Collected as part of a research study, without a referral diagnosis. Few moles overall by the patient's own estimate. A skin lesion imaged with a dermatoscope. The patient says their skin reddens with sun exposure. A male patient age 62 — 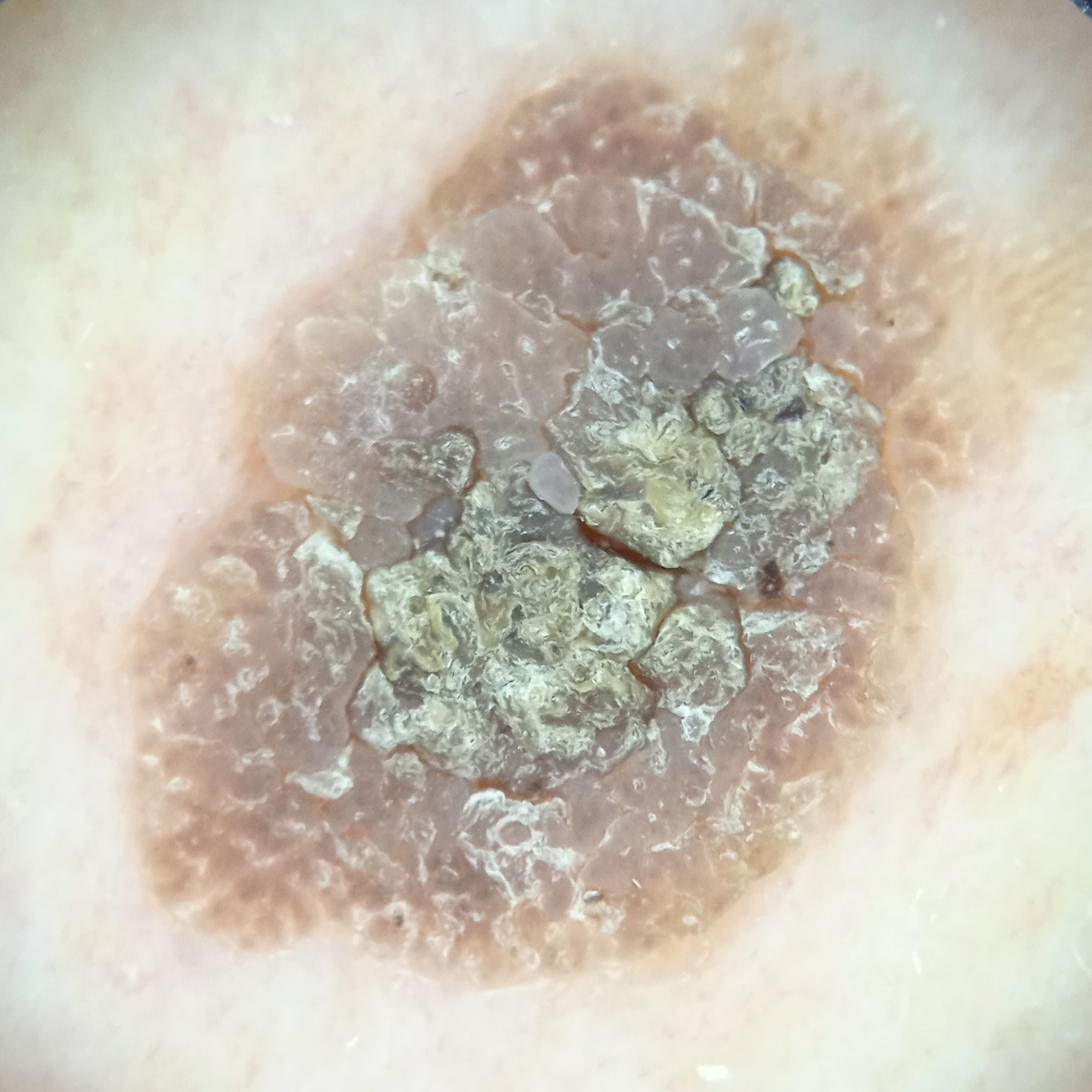anatomic site: the back | diameter: 10.9 mm | diagnostic label: seborrheic keratosis (dermatologist consensus).